A dermoscopic close-up of a skin lesion:
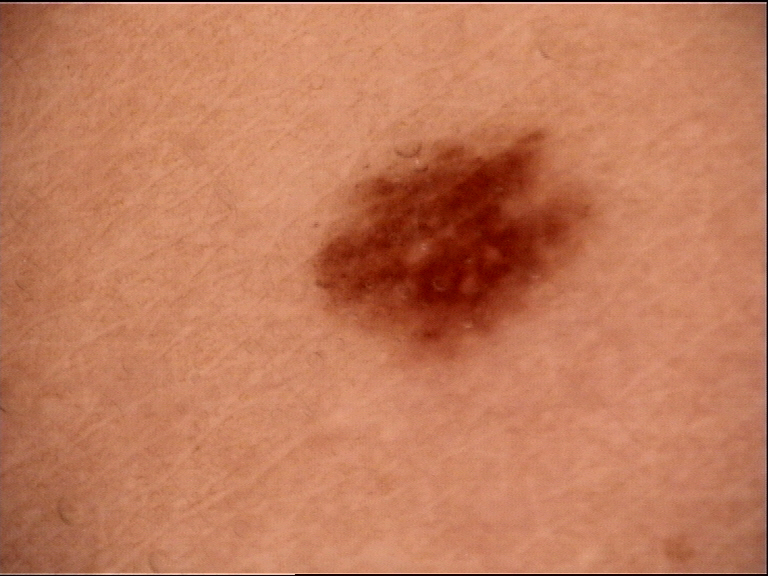| field | value |
|---|---|
| label | dysplastic junctional nevus (expert consensus) |